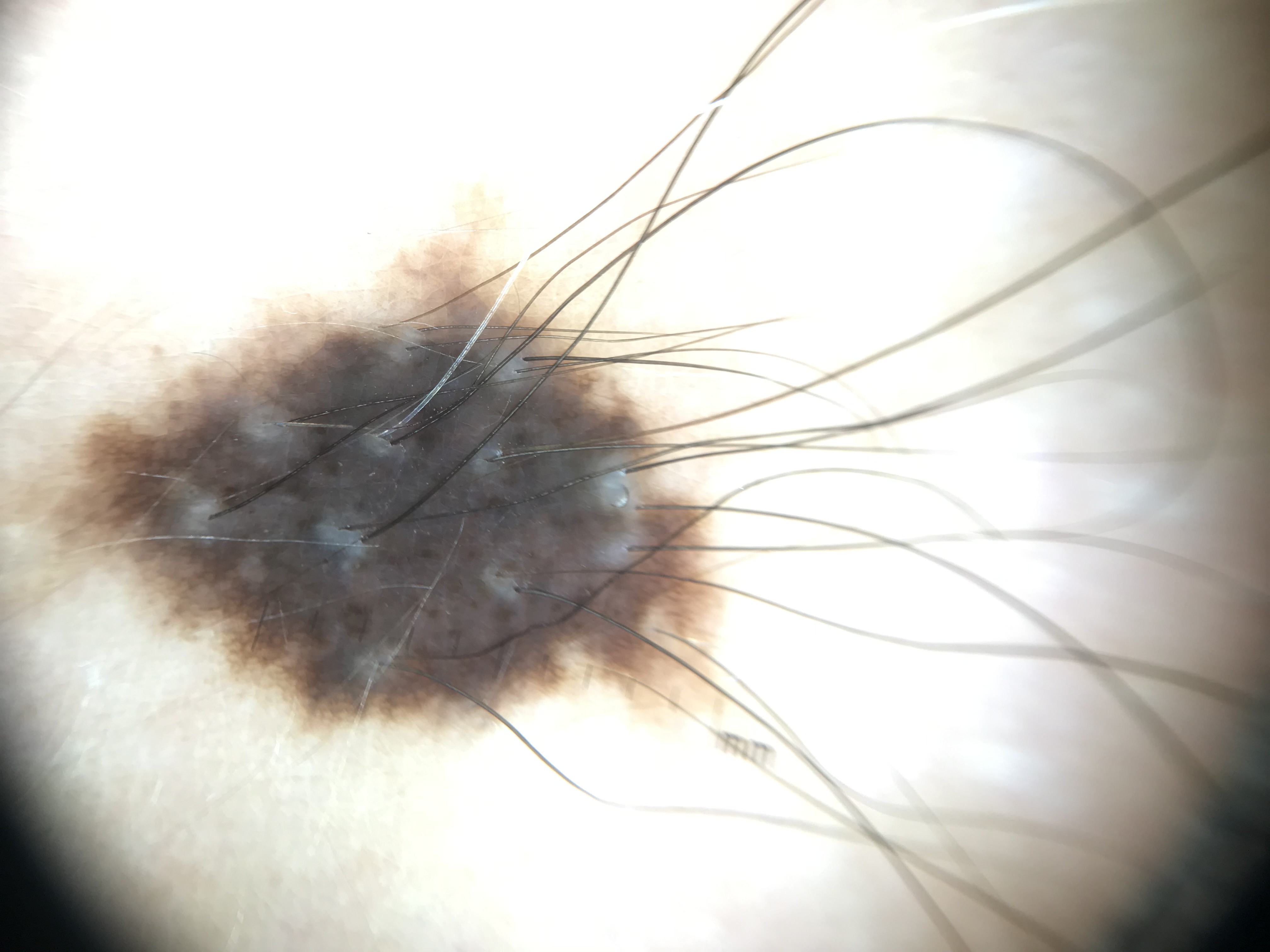Impression: Diagnosed as a congenital dysplastic compound nevus.